A dermoscopic view of a skin lesion · the patient is a female roughly 55 years of age — 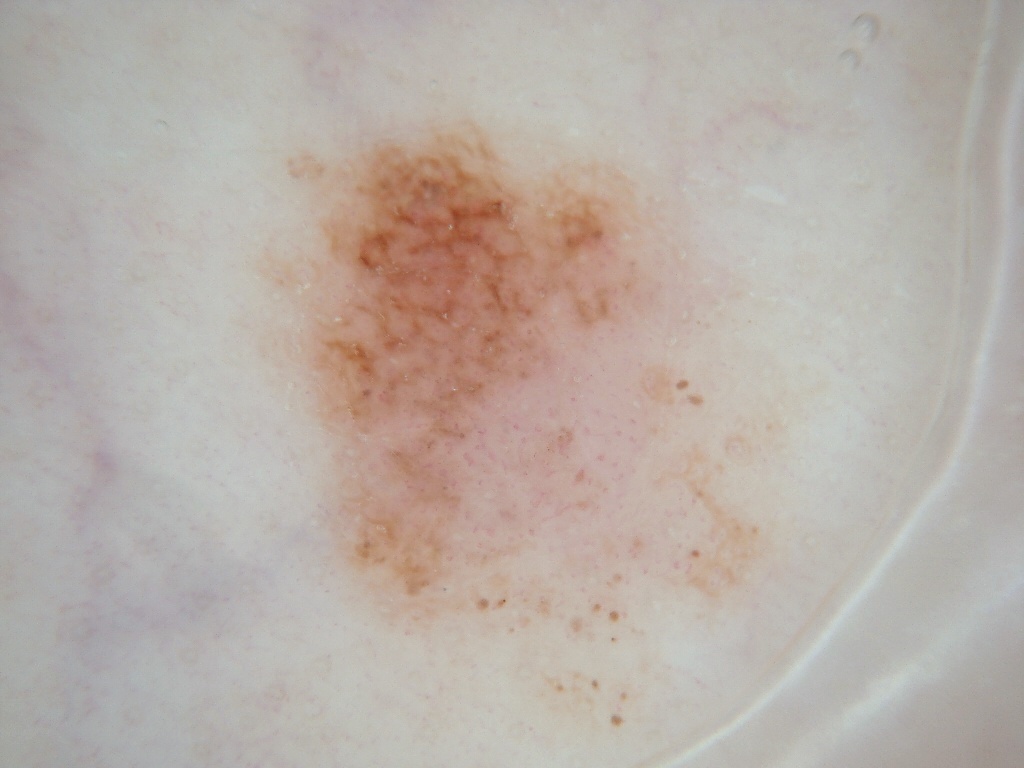The lesion occupies roughly 34% of the field. As (left, top, right, bottom), the lesion spans box(234, 103, 794, 755). Dermoscopy demonstrates globules and pigment network, with no streaks, milia-like cysts, or negative network. Expert review diagnosed this as a melanocytic nevus.